A dermoscopic image of a skin lesion.
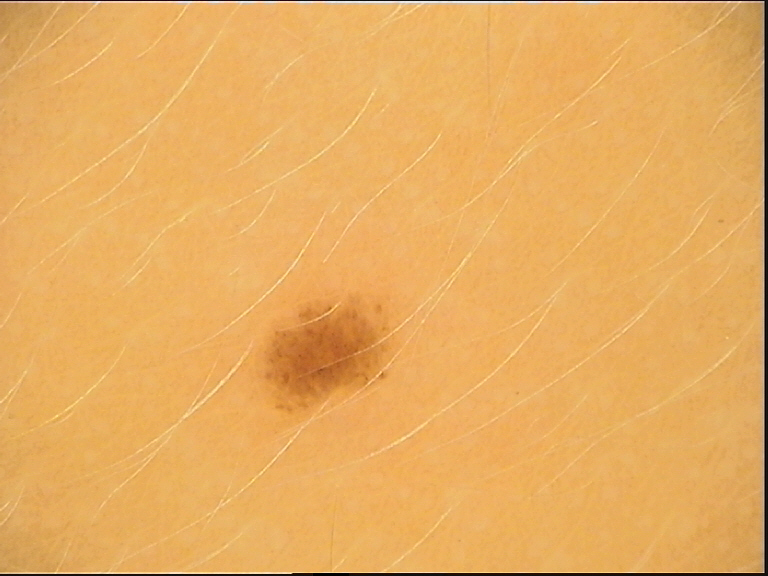<lesion>
<diagnosis>
<name>dysplastic junctional nevus</name>
<code>jd</code>
<malignancy>benign</malignancy>
<super_class>melanocytic</super_class>
<confirmation>expert consensus</confirmation>
</diagnosis>
</lesion>